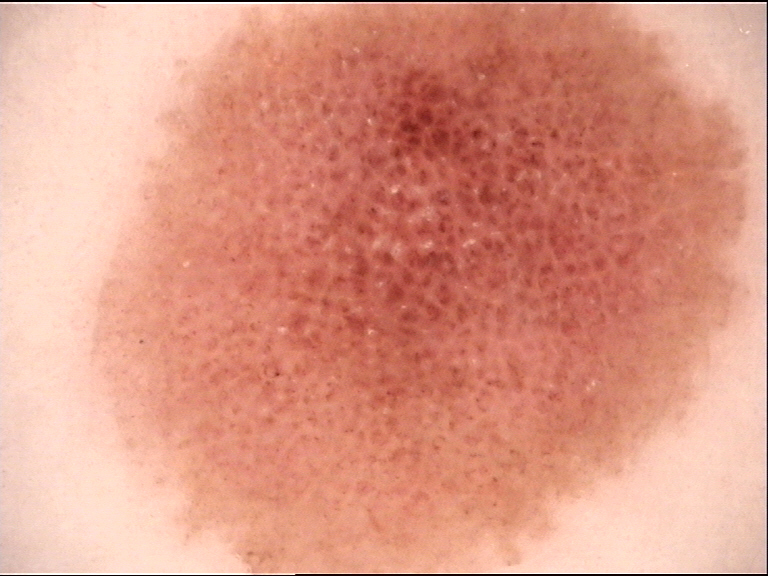Consistent with a benign lesion — a dysplastic junctional nevus.